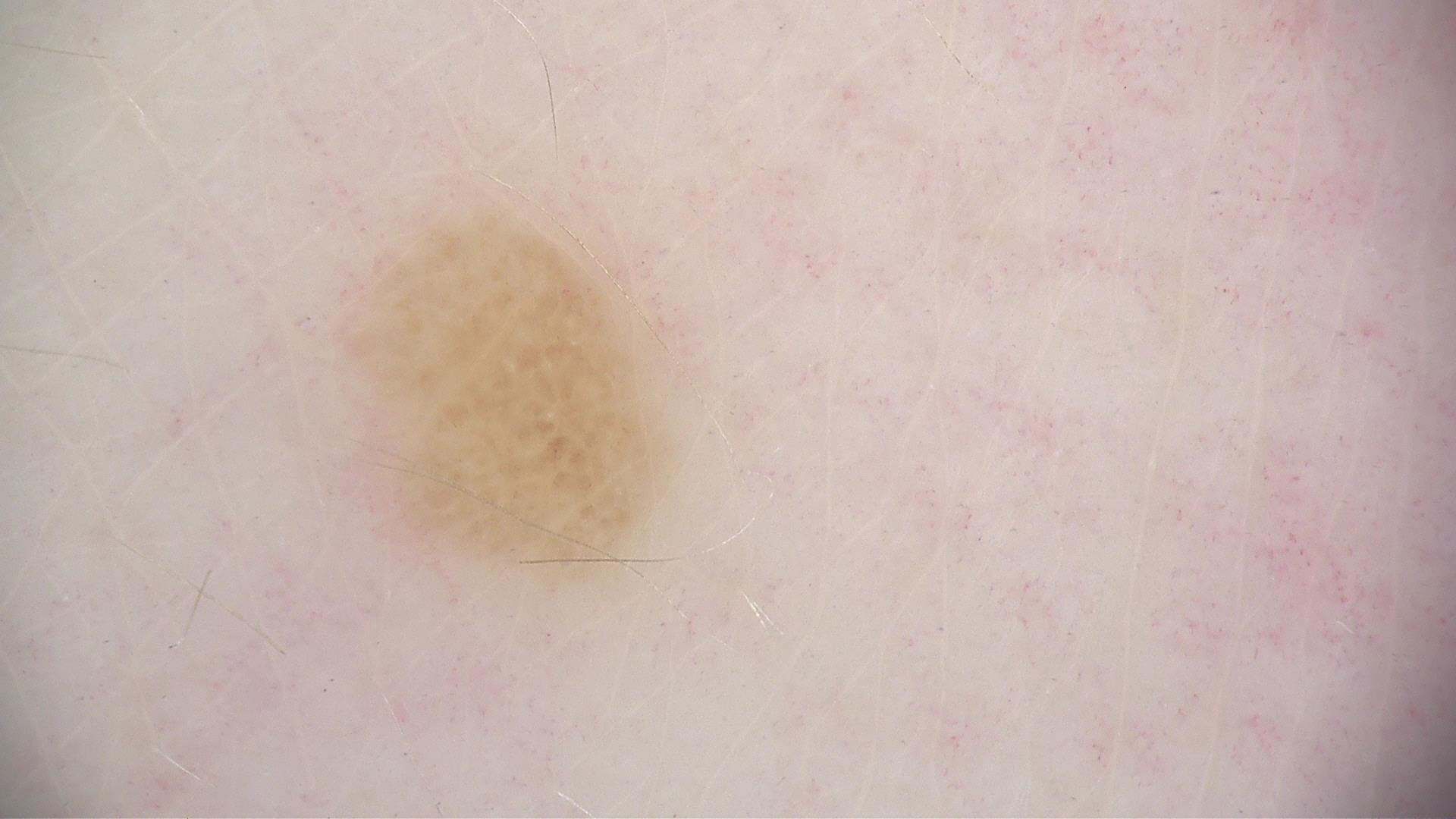This is a banal lesion. Consistent with a dermal nevus.